Located on the top or side of the foot; an image taken at an angle — 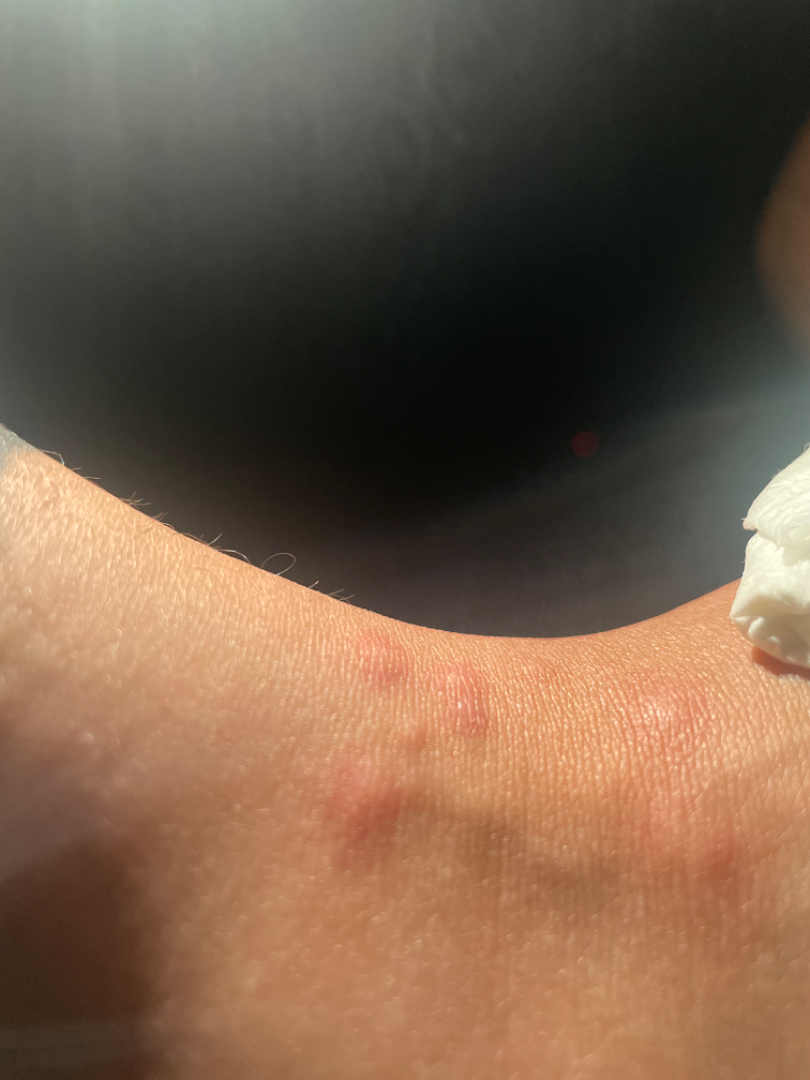Assessment:
Insect Bite (weight 1.00).